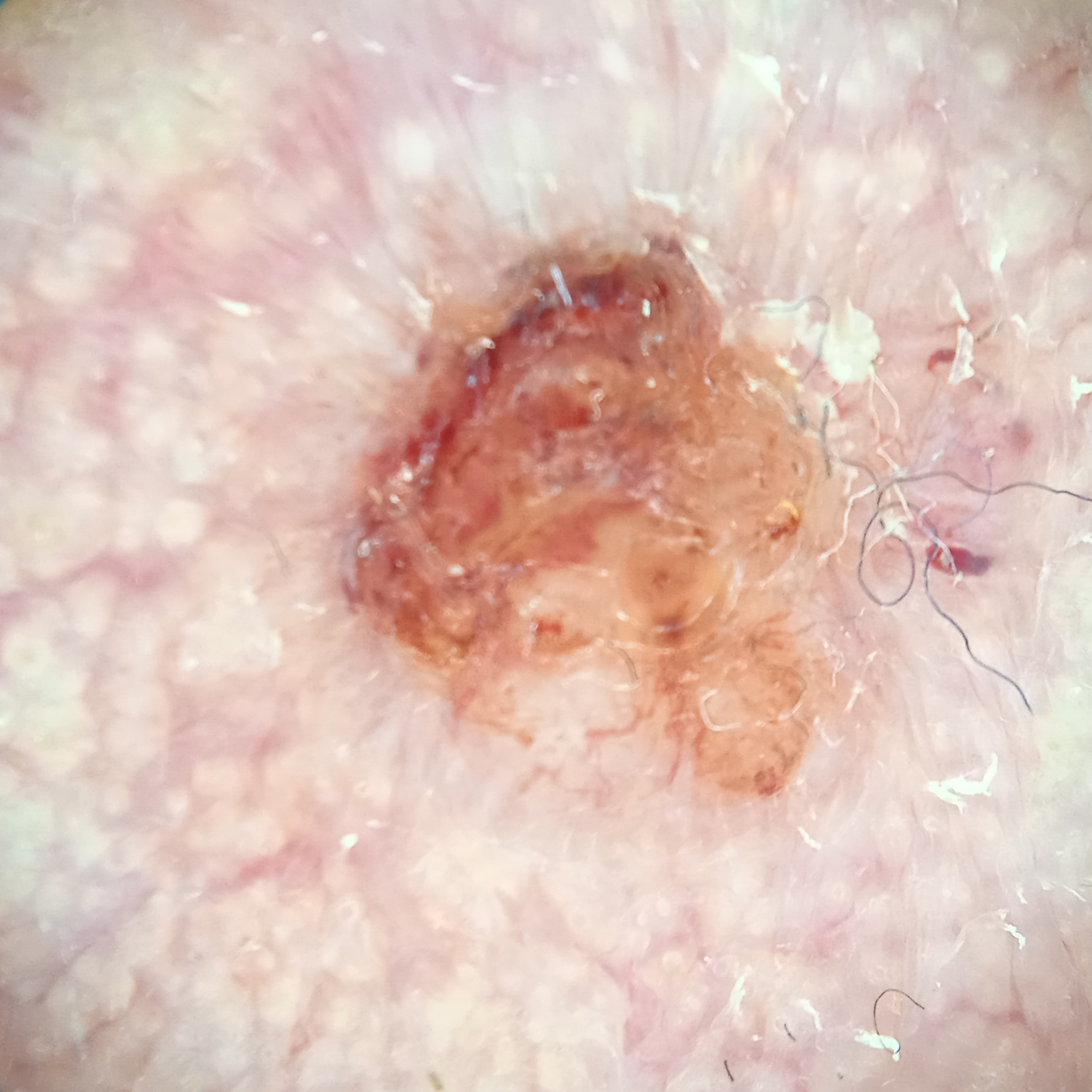Clinical context:
The patient reports no personal history of skin cancer. A skin lesion imaged with a dermatoscope. The patient says their skin reddens painfully with sun exposure. Referred with a clinical suspicion of basal cell carcinoma. A male subject 89 years of age. The lesion is located on the face. The lesion is about 8.5 mm across.
Diagnosis:
Histopathologically confirmed as a basal cell carcinoma, following excision, with tumor thickness 2.2 mm.